A male patient aged 38 to 42; a dermoscopy image of a single skin lesion: 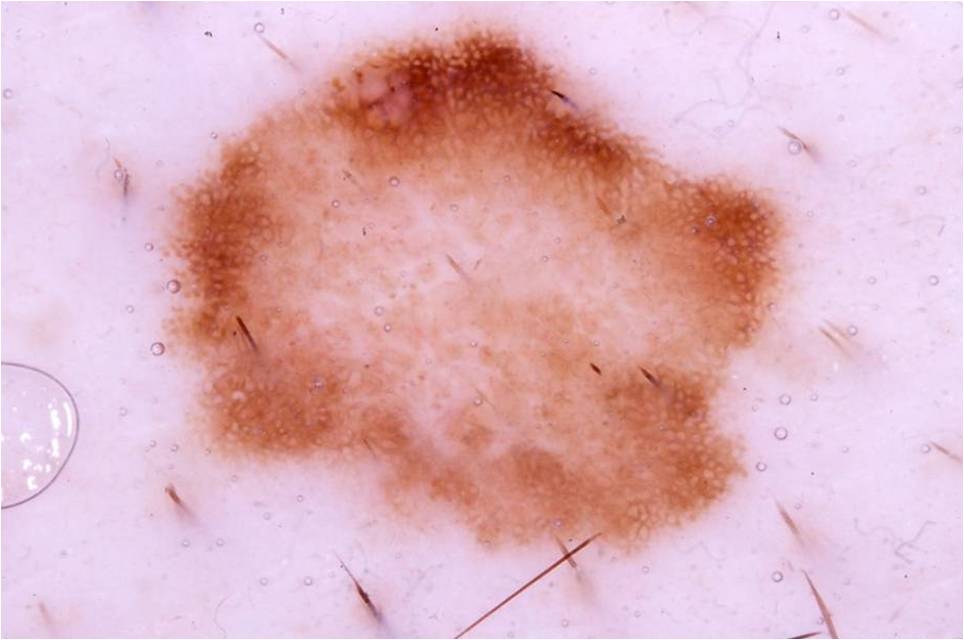Case summary:
- dermoscopic features — pigment network and globules
- size — ~41% of the field
- lesion location — 159/20/807/565
- diagnostic label — a melanoma